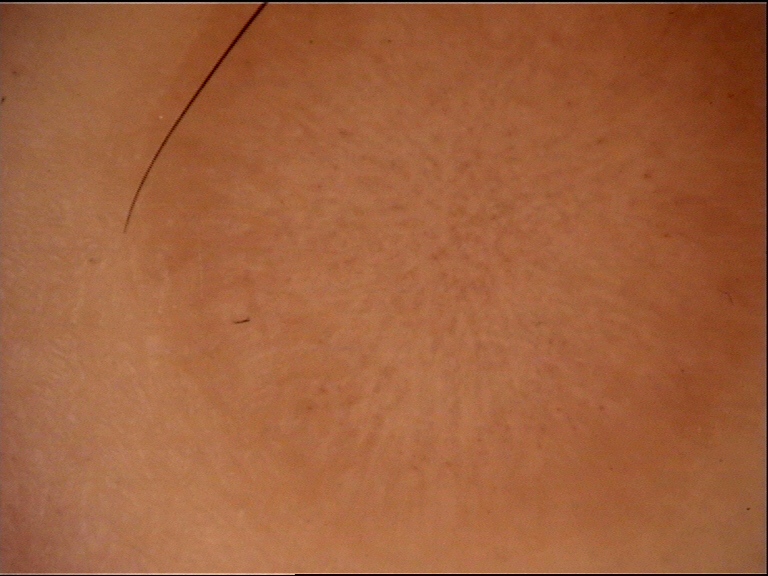Conclusion:
The diagnosis was a dermatofibroma.